A clinical photograph showing a skin lesion. The patient says their skin tans without first burning. By self-report, a personal history of cancer and a family history of skin cancer. Imaged for a research study, with no referral diagnosis recorded: 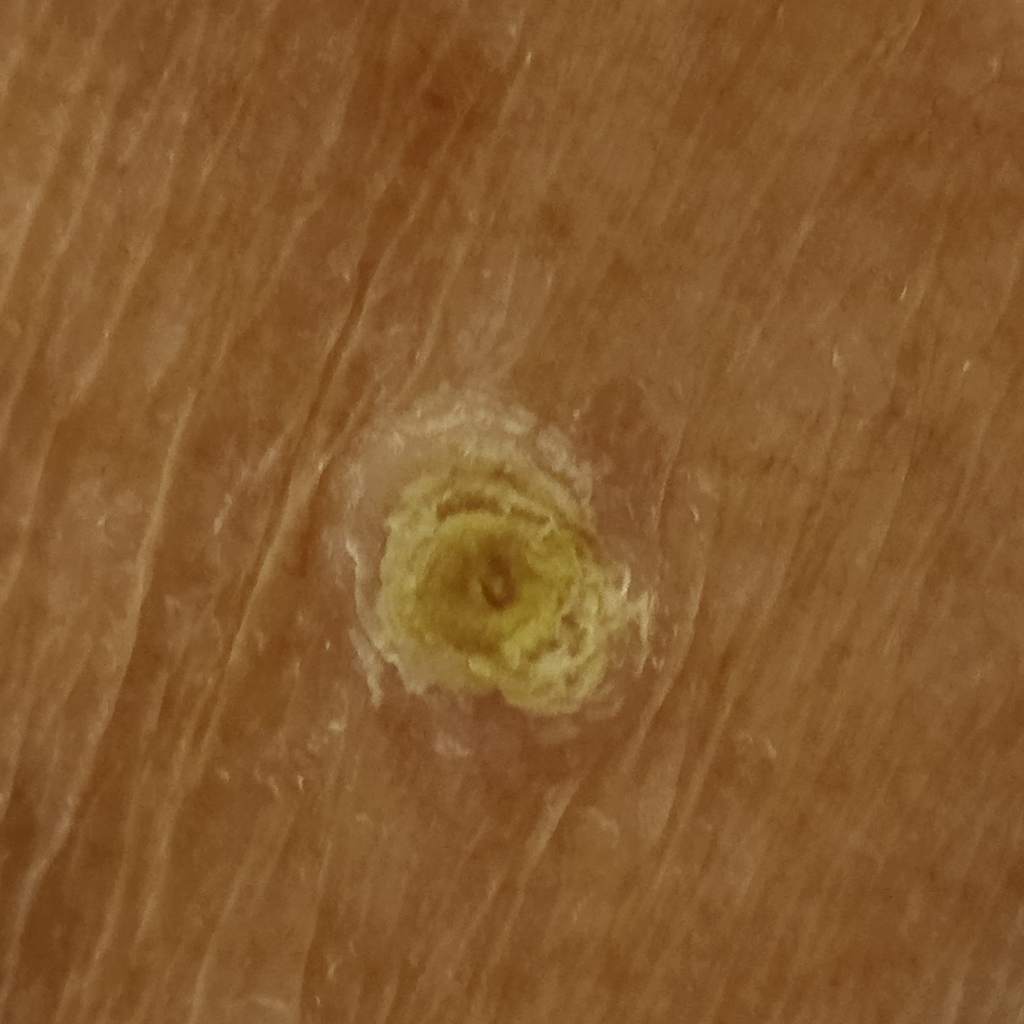Clinical context: The lesion is located on the torso. Measuring roughly 12.5 mm. Impression: The consensus diagnosis for this lesion was a squamous cell carcinoma.